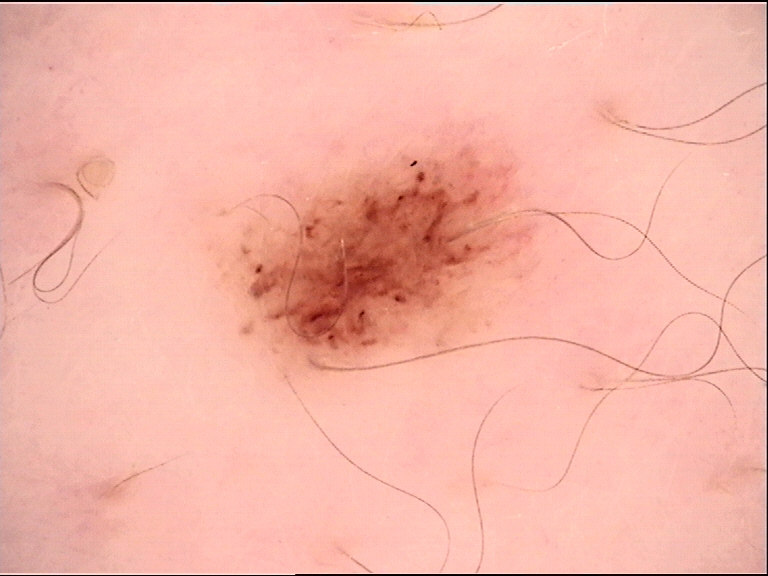  diagnosis:
    name: dysplastic junctional nevus
    code: jd
    malignancy: benign
    super_class: melanocytic
    confirmation: expert consensus